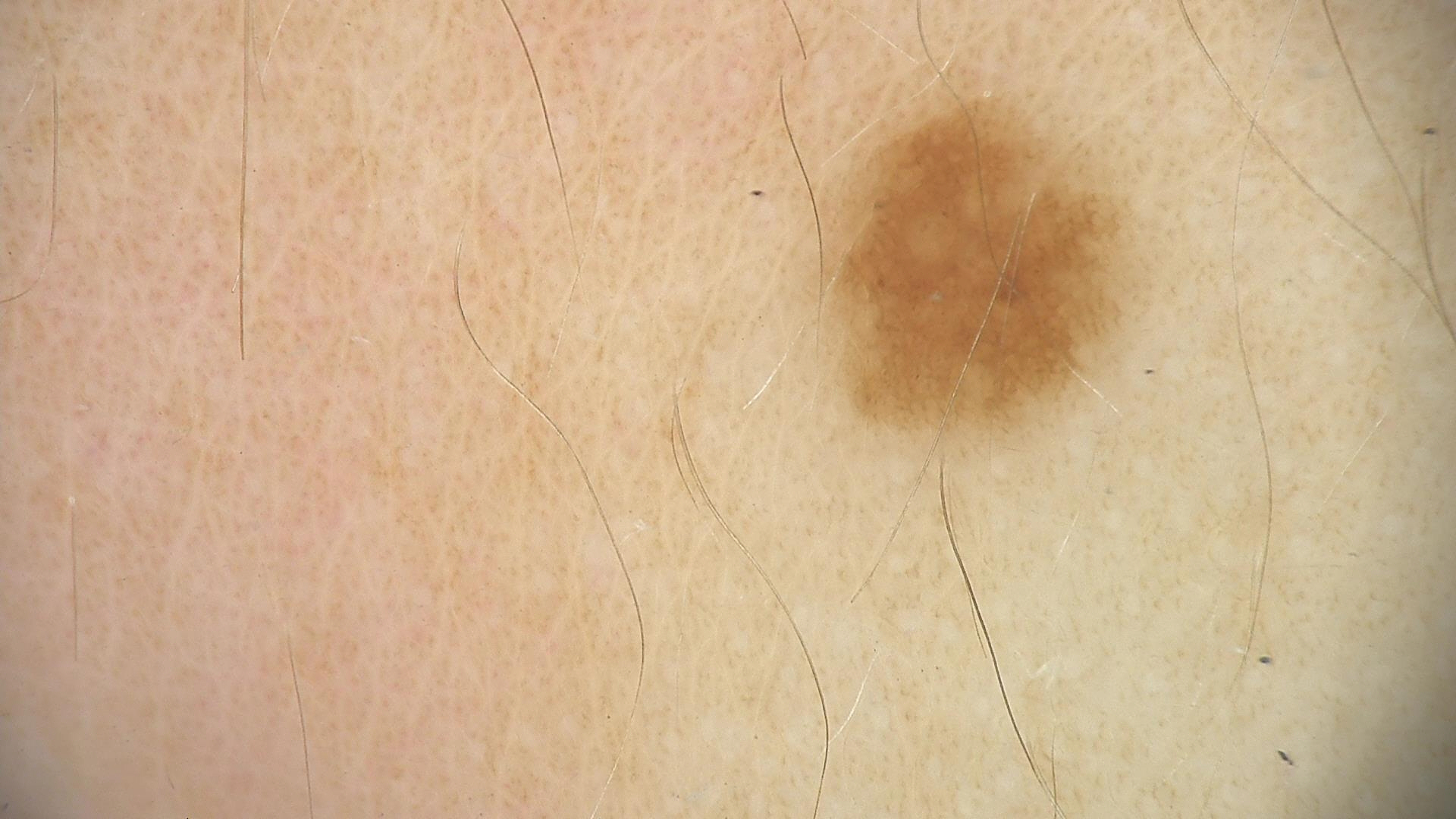- diagnostic label · dysplastic junctional nevus (expert consensus)